A dermoscopic view of a skin lesion; the patient is a male in their mid-50s: 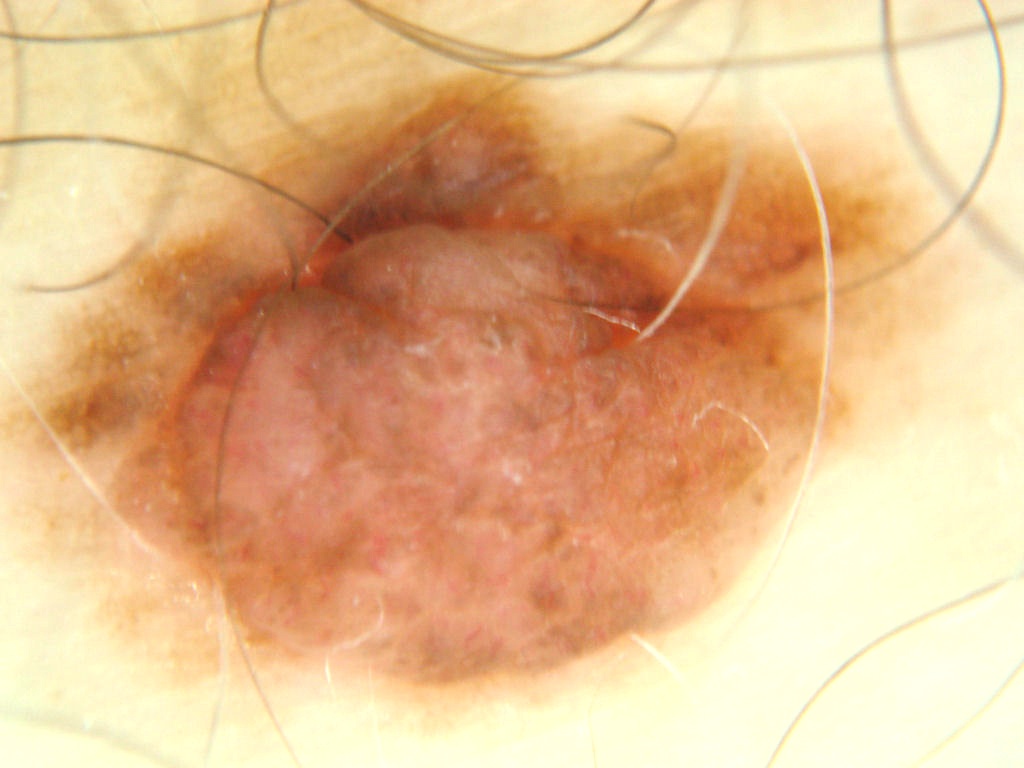The lesion's extent is x1=22 y1=59 x2=962 y2=730. Dermoscopically, the lesion shows pigment network. The clinical diagnosis was a melanocytic nevus, a benign lesion.